The patient notes bothersome appearance, itching and enlargement; the lesion involves the arm; the photograph is a close-up of the affected area; reported duration is less than one week; texture is reported as rough or flaky.
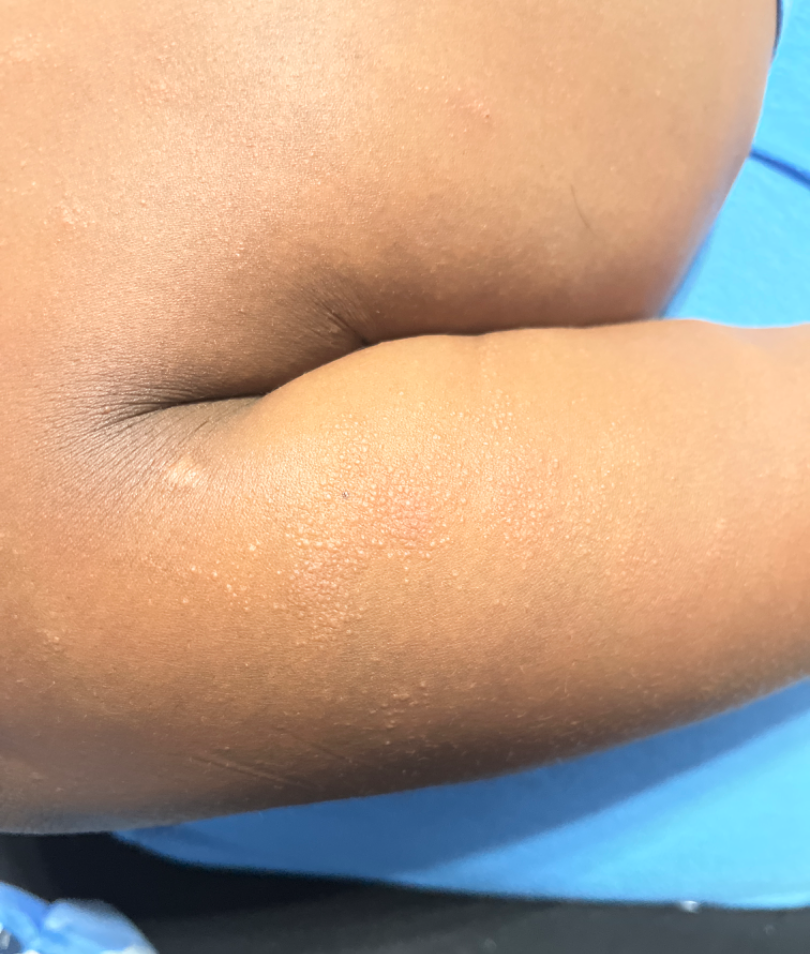{
  "differential": {
    "leading": [
      "Miliaria"
    ]
  }
}